Skin tone: FST IV. An image taken at an angle — 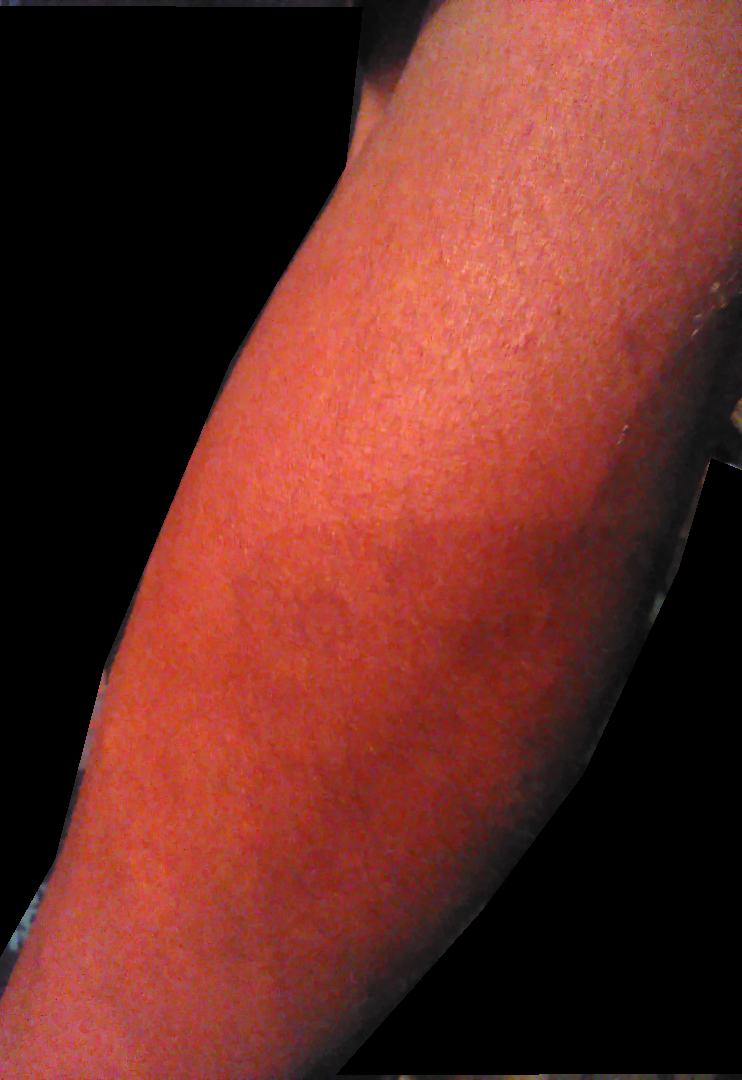Hypersensitivity (possible); Allergic Contact Dermatitis (possible).